A dermatoscopic image of a skin lesion: 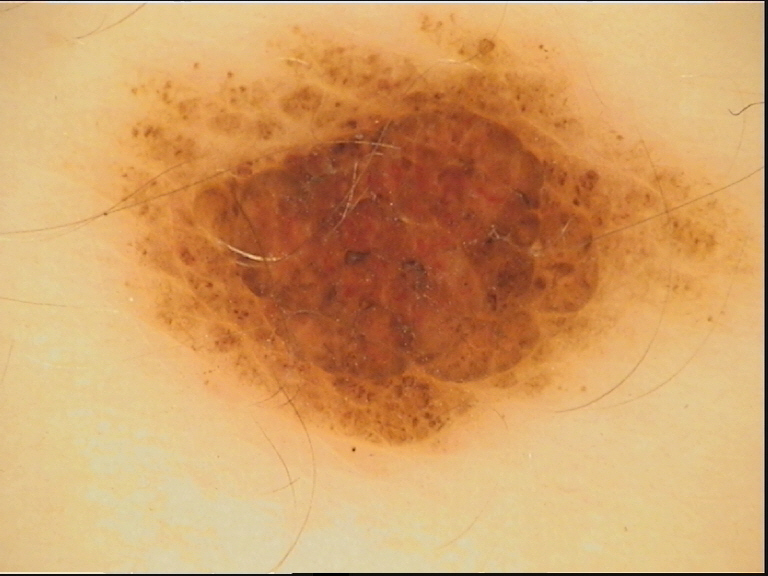<lesion>
<lesion_type>
<main_class>banal</main_class>
<pattern>compound</pattern>
</lesion_type>
<diagnosis>
<name>compound nevus</name>
<code>cb</code>
<malignancy>benign</malignancy>
<super_class>melanocytic</super_class>
<confirmation>expert consensus</confirmation>
</diagnosis>
</lesion>